A skin lesion imaged with a dermatoscope: 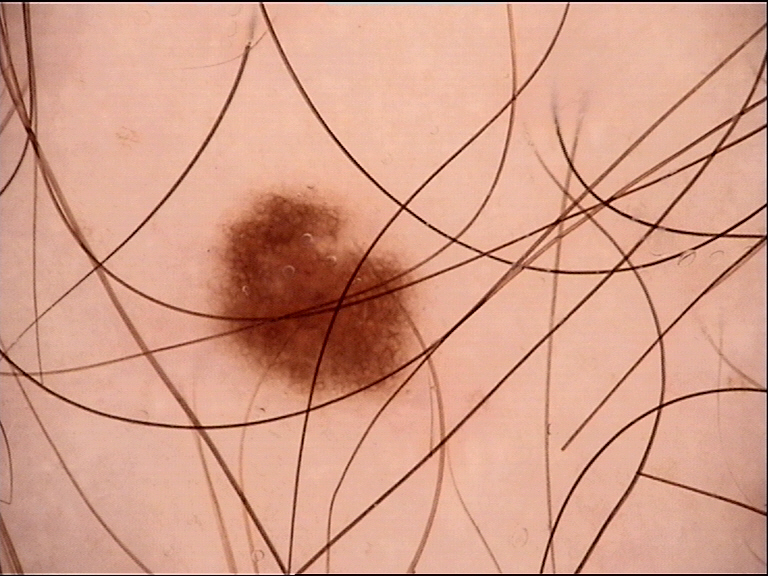class — dysplastic junctional nevus (expert consensus).